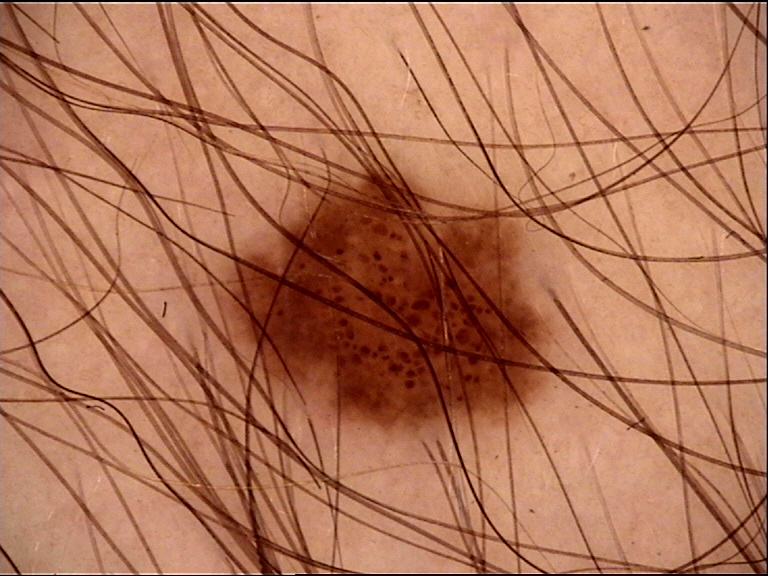{
  "lesion_type": {
    "main_class": "banal",
    "pattern": "junctional"
  },
  "diagnosis": {
    "name": "junctional nevus",
    "code": "jb",
    "malignancy": "benign",
    "super_class": "melanocytic",
    "confirmation": "expert consensus"
  }
}